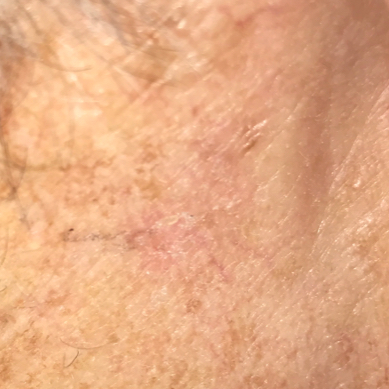A clinical photo of a skin lesion taken with a smartphone. A male patient aged 77. The lesion was found on the neck. Clinically diagnosed as an actinic keratosis.